A close-up photograph; the lesion involves the head or neck — 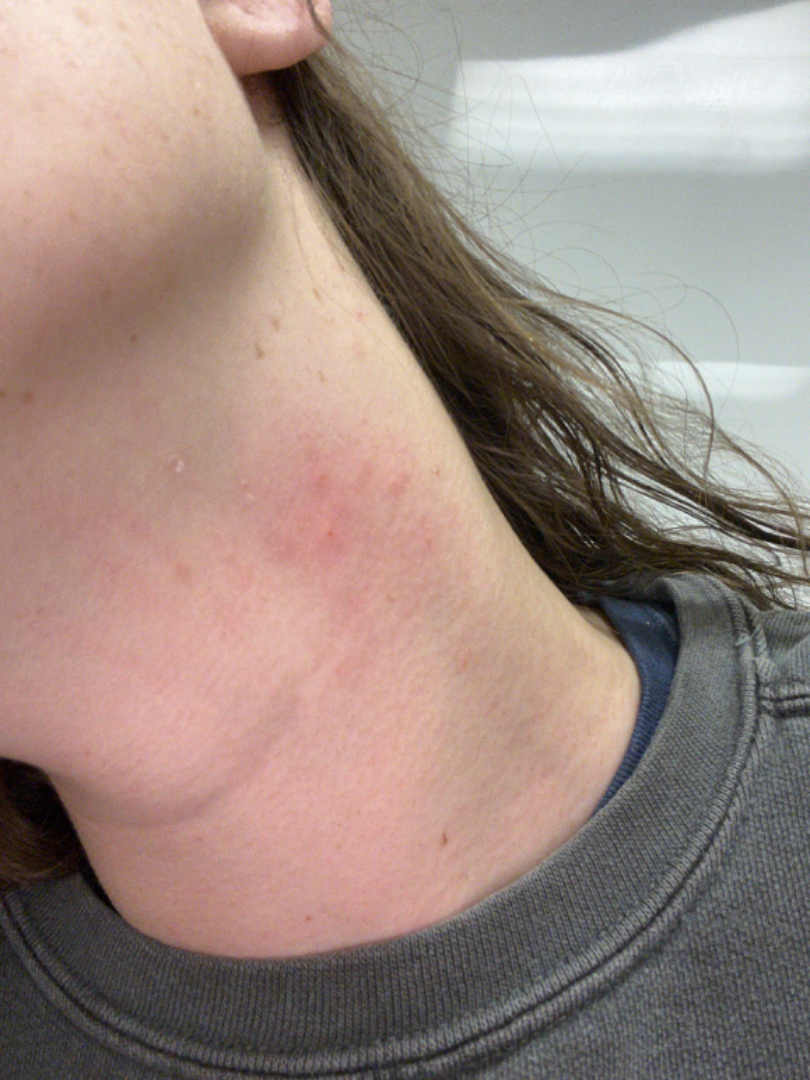A single dermatologist reviewed the case: Allergic Contact Dermatitis and Irritant Contact Dermatitis were considered with similar weight.